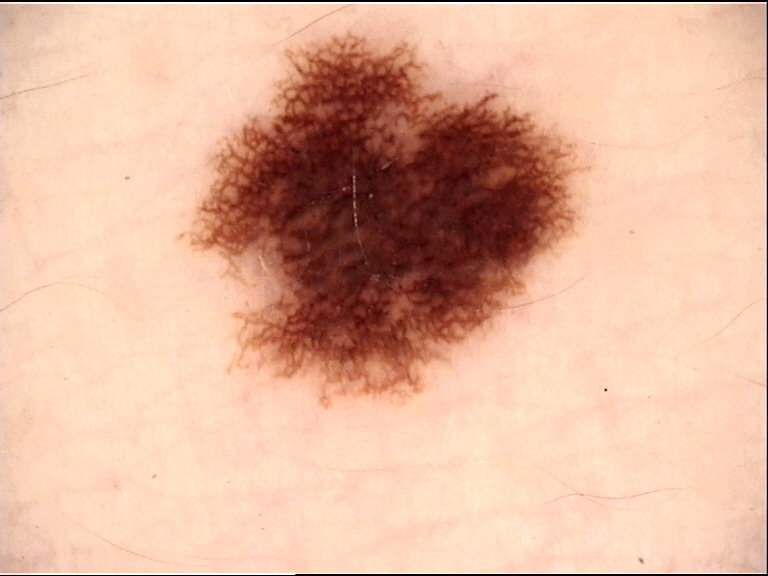Conclusion: Labeled as a dysplastic junctional nevus.